Female patient, age 18–29 · the patient indicates burning, itching and pain · the photograph is a close-up of the affected area · the lesion involves the palm · present for one to four weeks · the patient indicates the lesion is raised or bumpy, fluid-filled and rough or flaky.
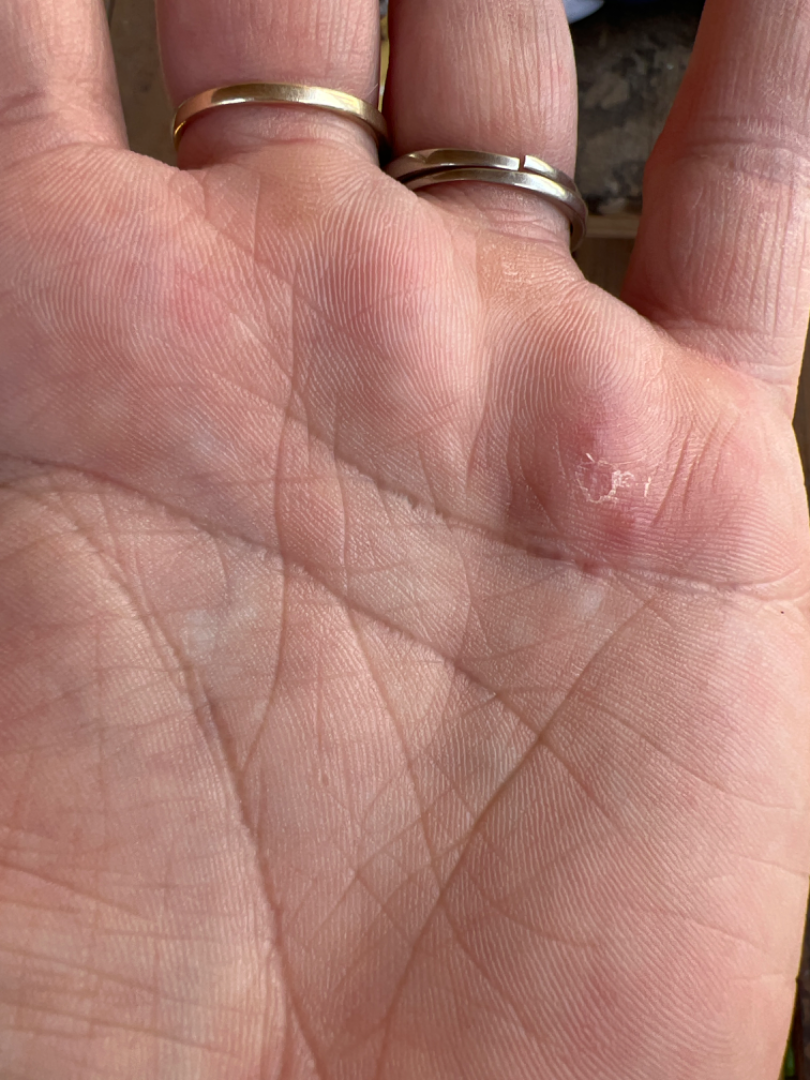On dermatologist assessment of the image, Clavus (leading); Impetigo (considered); Foreign body (considered); Herpes Simplex (considered).